A dermoscopic close-up of a skin lesion: 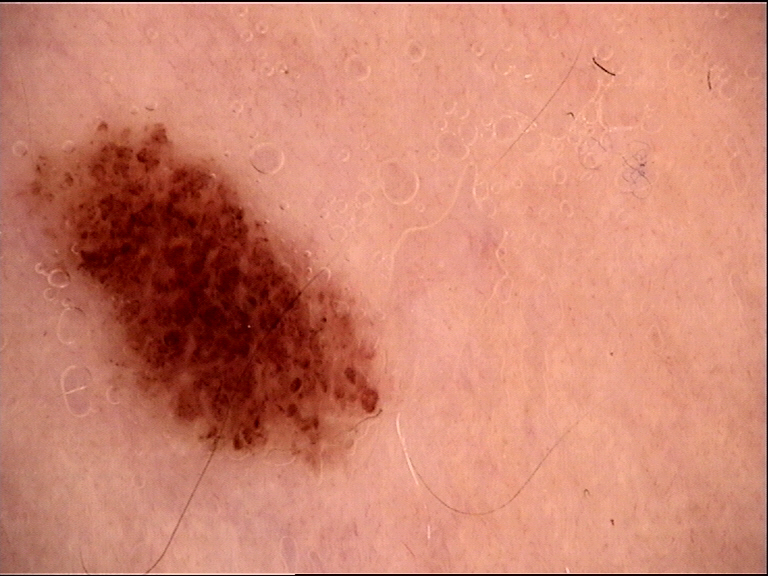Case: This is a banal lesion. Impression: The diagnostic label was a compound nevus.